Female contributor, age 40–49; the leg is involved; the photograph was taken at a distance — 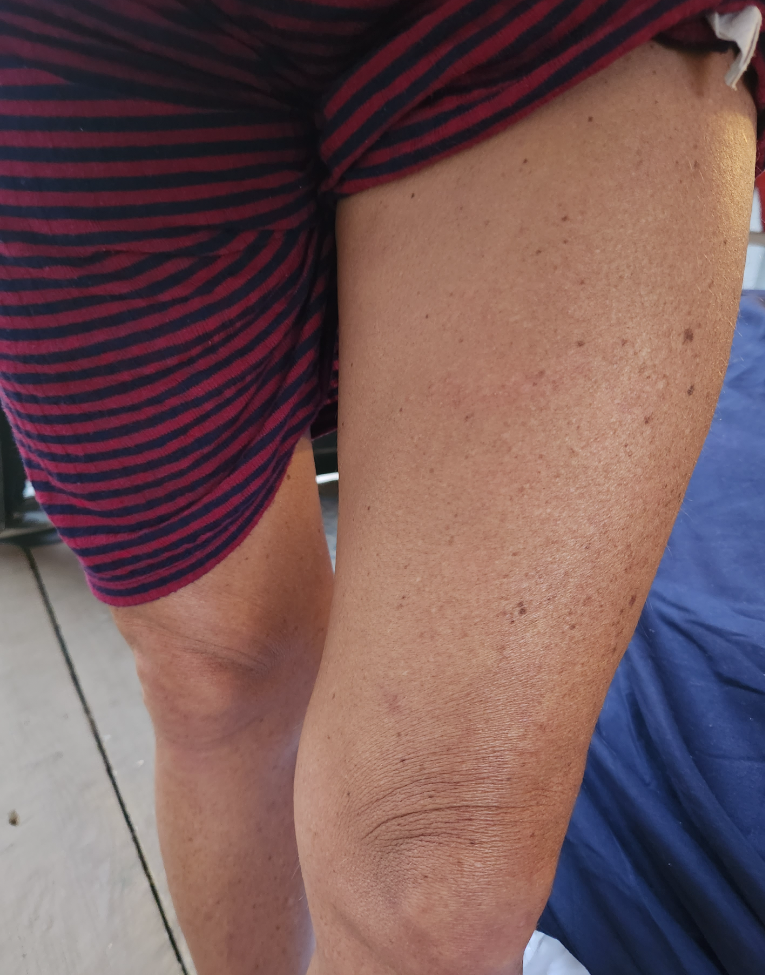Findings:
• diagnostic considerations — Folliculitis (primary); Keratosis pilaris (considered); Lichen spinulosus (considered)